Few moles overall by the patient's own estimate. The patient reports a personal history of cancer and a personal history of skin cancer. Referred for assessment of suspected basal cell carcinoma. A clinical photograph showing a skin lesion: 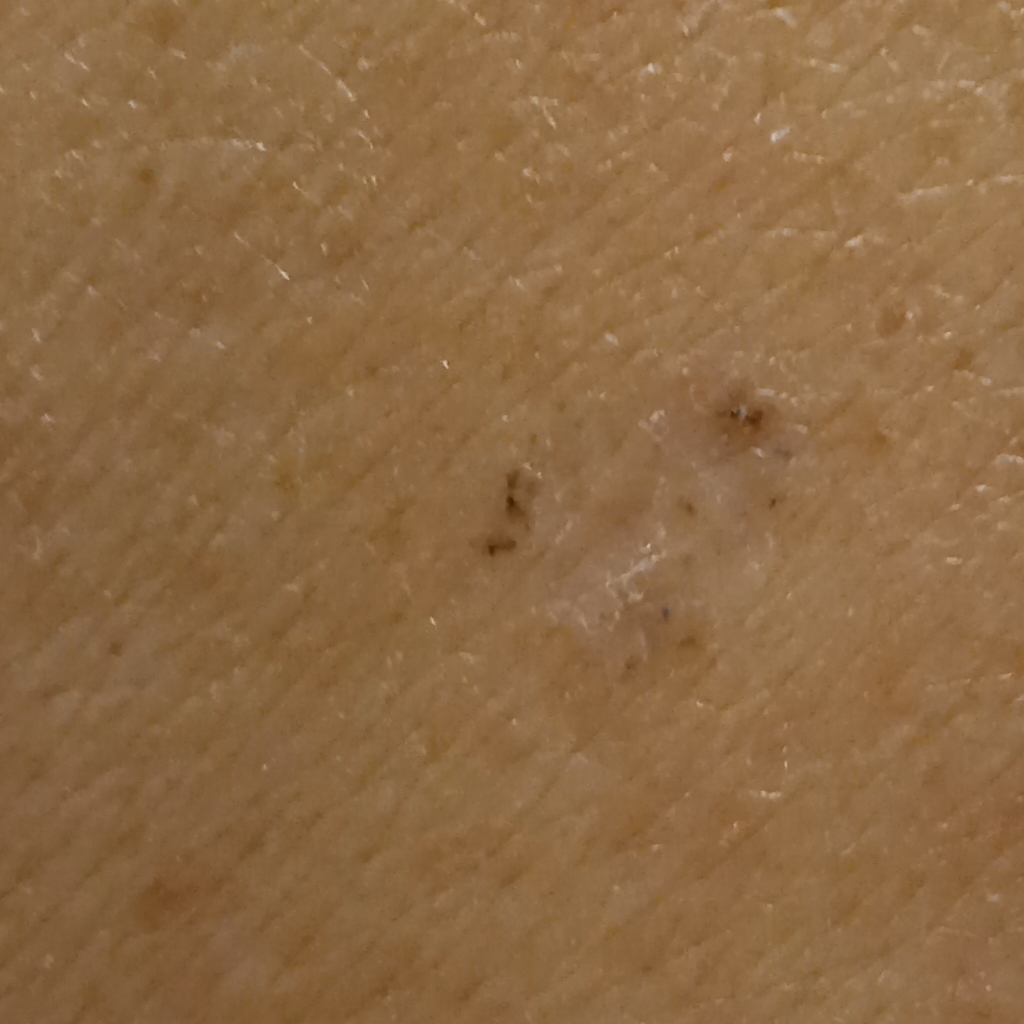Findings:
– site · the back
– size · 7.8 mm
– diagnostic label · basal cell carcinoma (dermatologist consensus)